Close-up view, the affected area is the back of the hand:
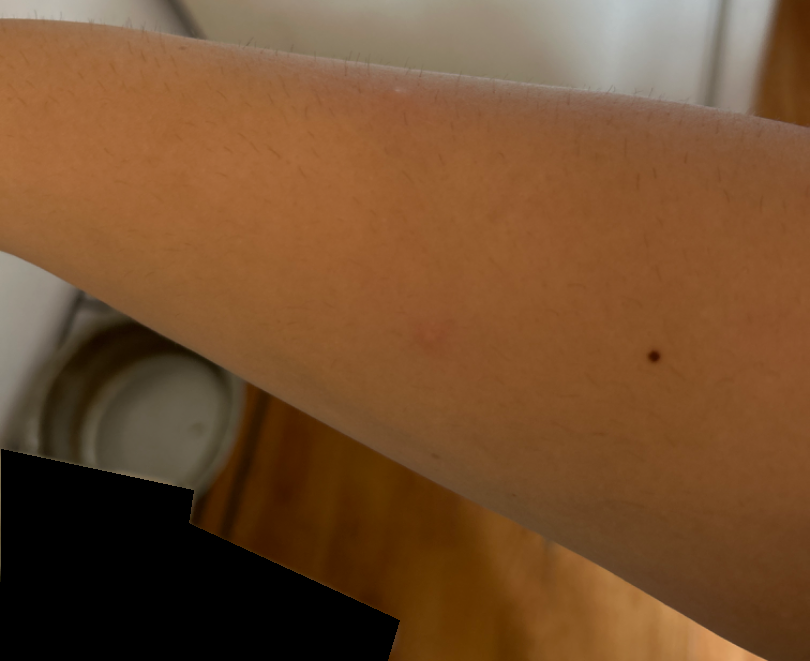Background: The lesion is described as raised or bumpy. Reported duration is one to four weeks. The patient considered this a rash. Findings: On photographic review by a dermatologist, most consistent with Insect Bite; with consideration of Folliculitis.